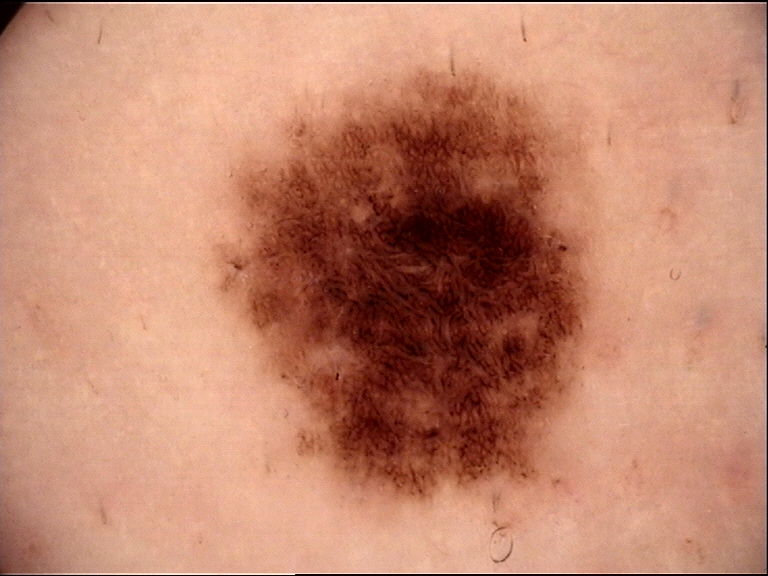Summary:
Dermoscopy of a skin lesion.
Impression:
Diagnosed as a dysplastic junctional nevus.